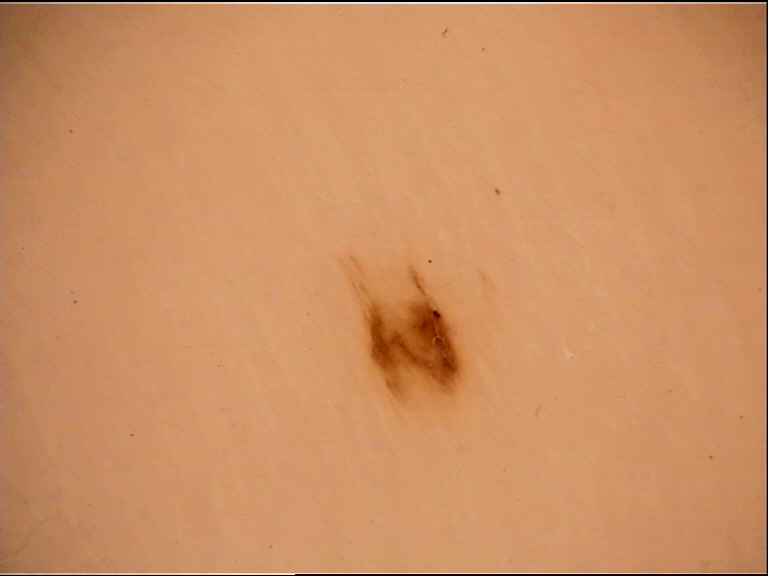A dermoscopy image of a single skin lesion. Consistent with an acral dysplastic junctional nevus.